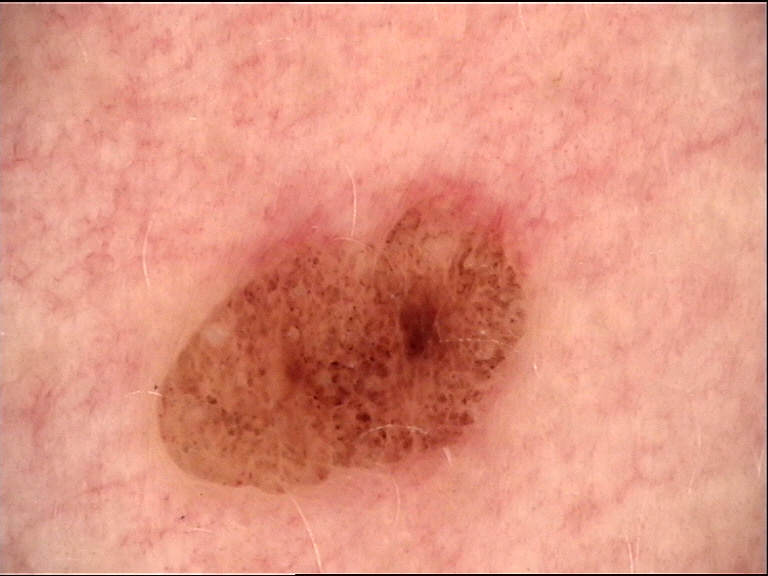A dermoscopic image of a skin lesion. The architecture is that of a banal lesion. Classified as a dermal nevus.